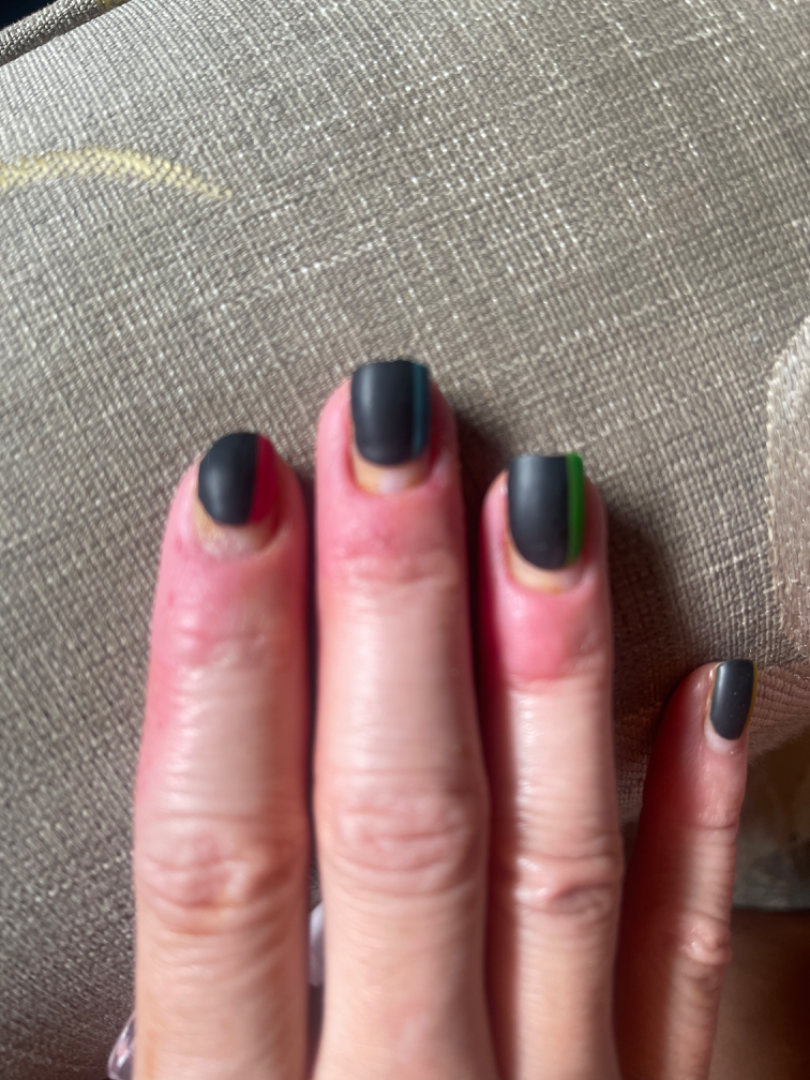The patient reports the lesion is raised or bumpy and rough or flaky.
Female patient, age 40–49.
No constitutional symptoms were reported.
Skin tone: Fitzpatrick skin type II; human graders estimated a MST of 2.
The patient considered this a nail problem.
The affected area is the palm.
The photograph is a close-up of the affected area.
On teledermatology review, favoring Paronychia; lower on the differential is Eczema; a more distant consideration is Allergic Contact Dermatitis.